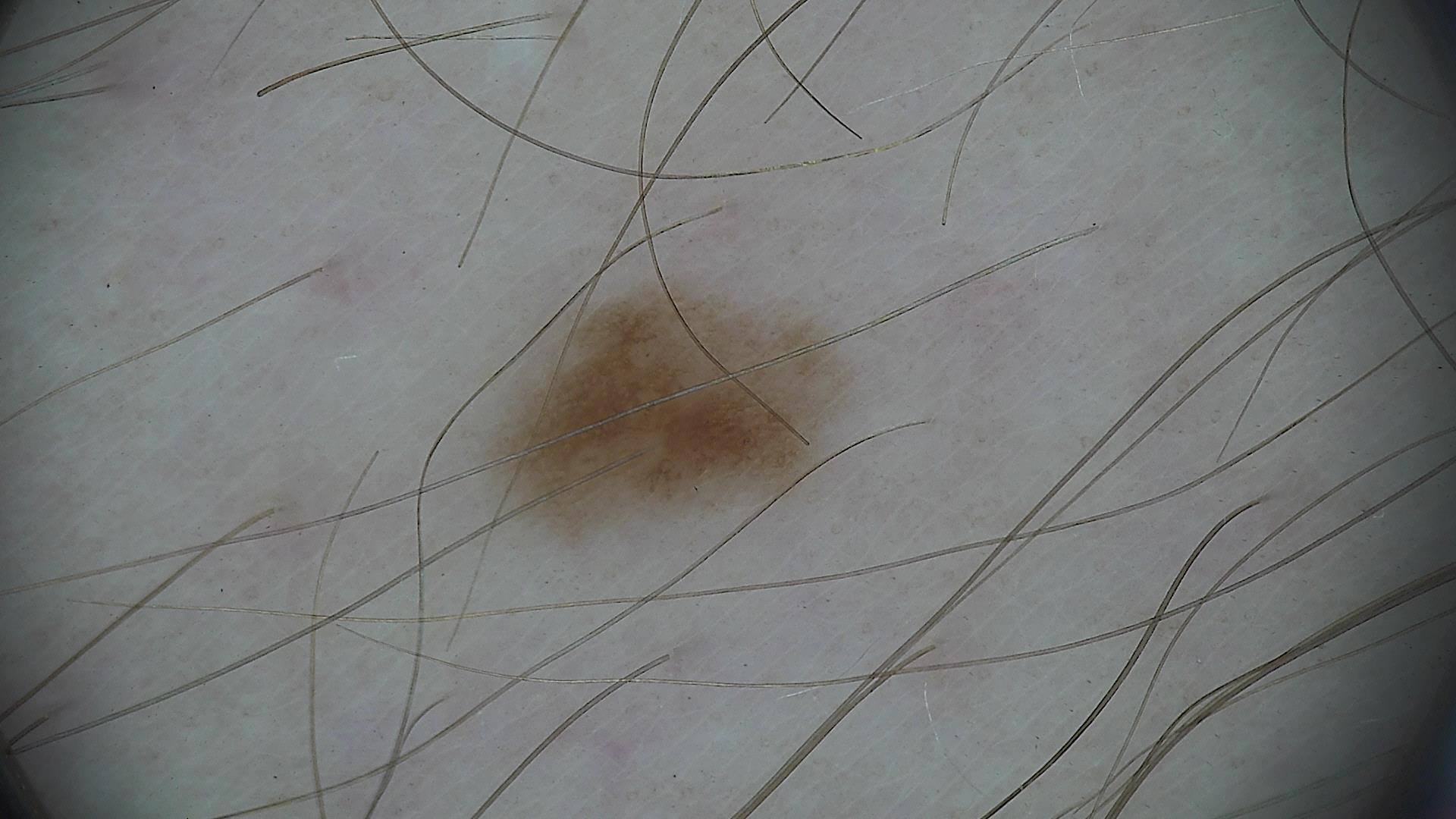Dermoscopy of a skin lesion. Consistent with a dysplastic junctional nevus.